The lesion involves the leg, the photograph was taken at a distance — 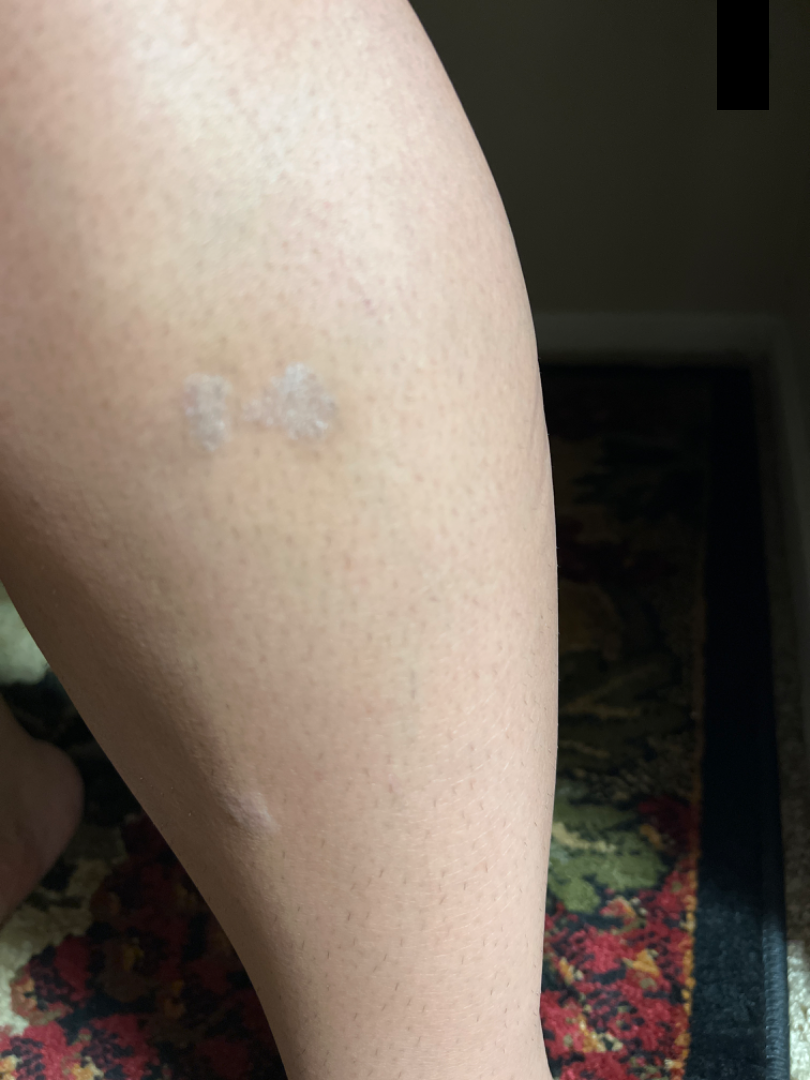• symptom duration — more than five years
• skin tone — FST IV; lay reviewers estimated Monk skin tone scale 1 or 3
• clinical impression — in keeping with Lichen planus/lichenoid eruption